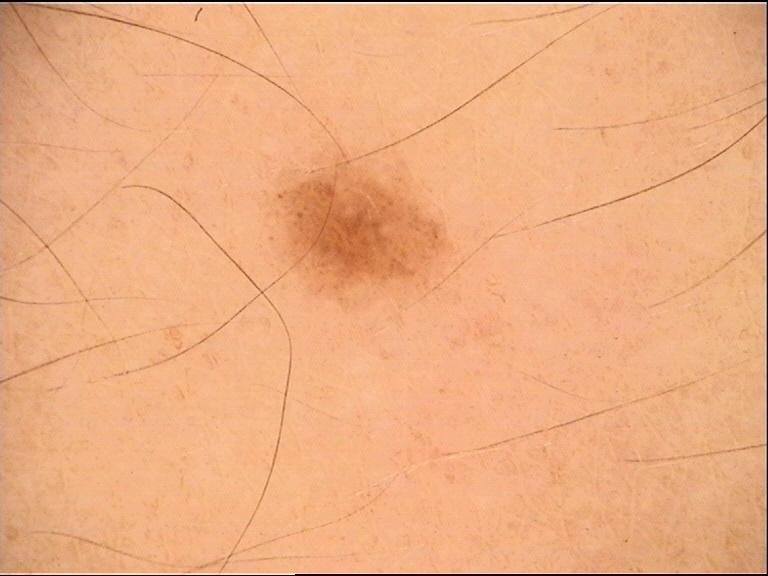Case: A dermoscopic image of a skin lesion. Conclusion: The diagnosis was a dysplastic compound nevus.